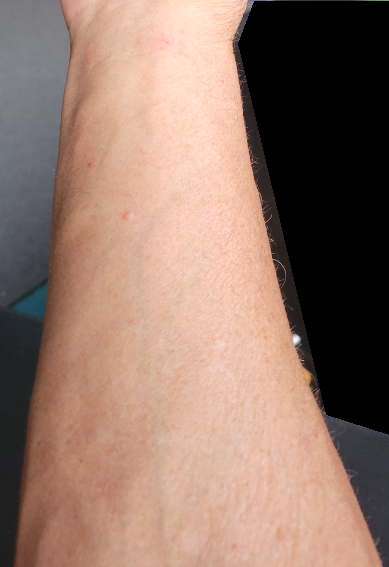Notes:
* assessment — could not be assessed
* site — arm
* symptoms — itching
* patient's own categorization — skin that appeared healthy to them
* subject — male, age 60–69
* present for — less than one week
* shot type — at a distance
* lesion texture — raised or bumpy